Acquired for a research image collection, with no referral diagnosis; the patient says their skin reddens painfully with sun exposure; a female patient age 35; the patient describes having a moderate number of moles:
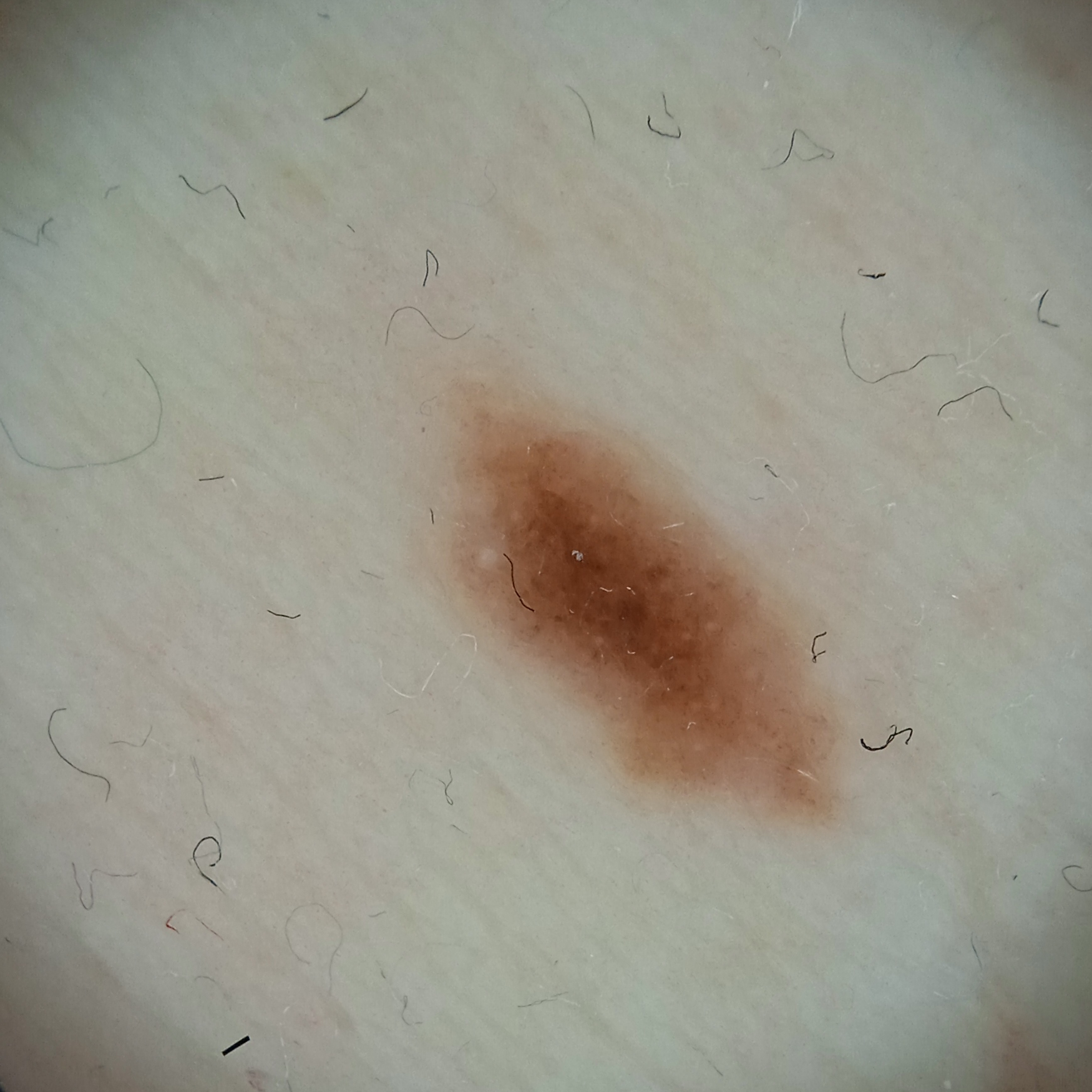Summary:
The lesion involves the torso. The lesion is about 6.3 mm across.
Assessment:
The consensus diagnosis for this lesion was a melanocytic nevus.